A dermoscopic close-up of a skin lesion, the subject is female — 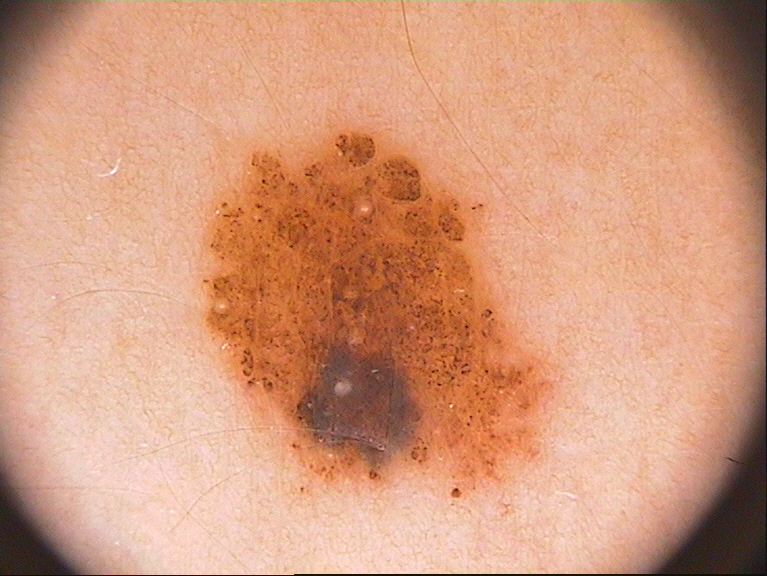Case summary:
– dermoscopic findings — globules
– bounding box — 193 126 562 506
– assessment — a melanocytic nevus